Located on the arm and front of the torso · an image taken at a distance:
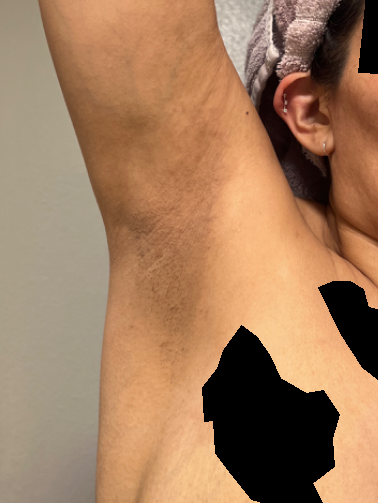| field | value |
|---|---|
| systemic symptoms | none reported |
| patient-reported symptoms | burning, bothersome appearance, itching, enlargement and darkening |
| texture | raised or bumpy |
| history | less than one week |
| patient's own categorization | a rash |
| differential | Allergic Contact Dermatitis (weight 0.67); Irritant Contact Dermatitis (weight 0.33) |